A skin lesion imaged with a dermatoscope:
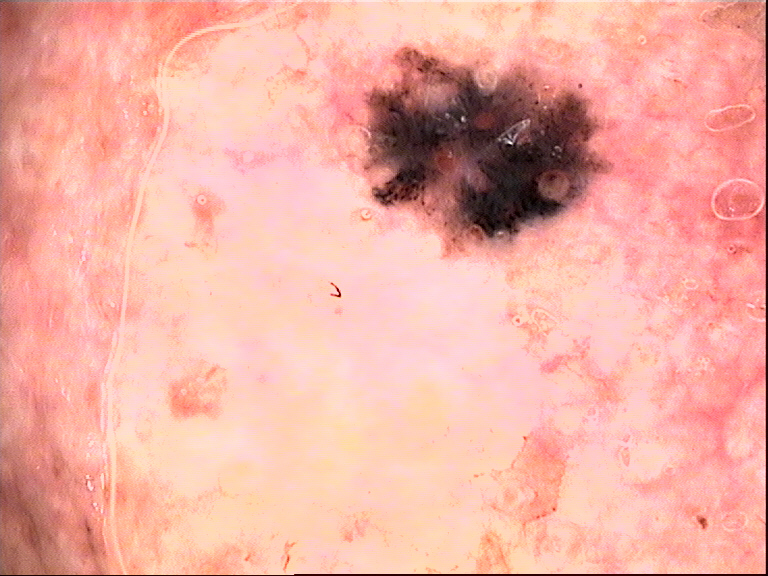Biopsy-confirmed as a keratinocytic lesion — a basal cell carcinoma.